The contributor is a female aged 50–59 · the photograph is a close-up of the affected area · the affected area is the arm and head or neck — 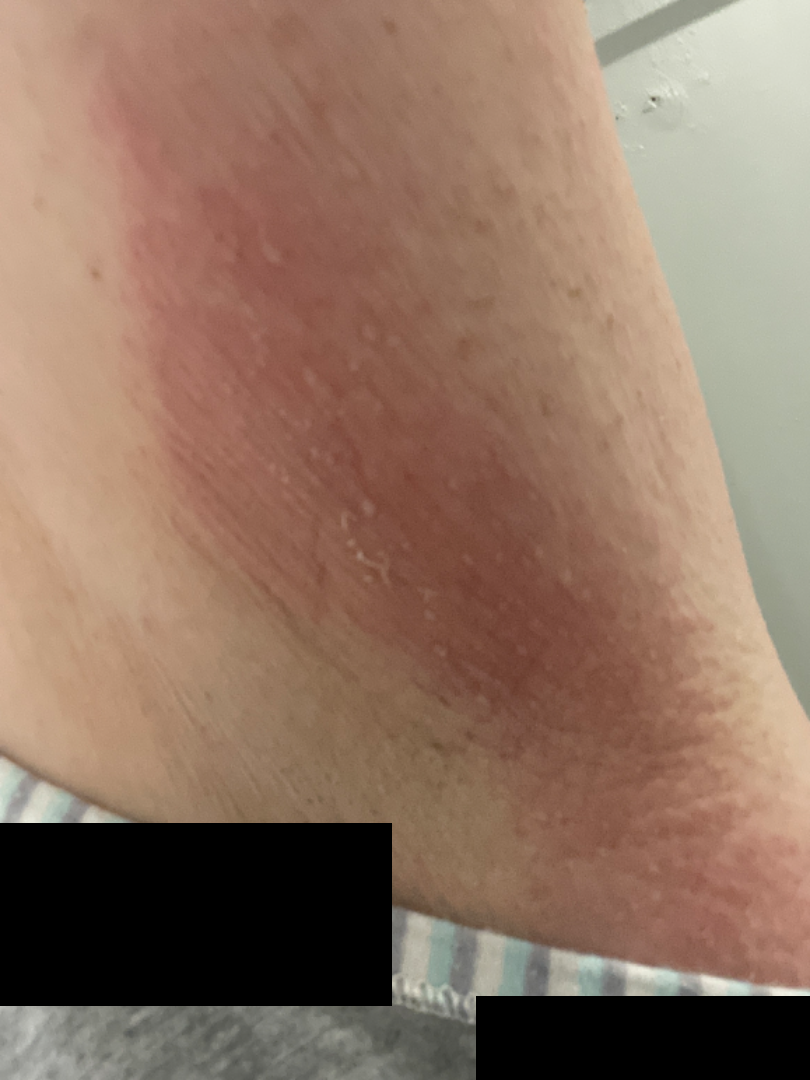Case summary:
- differential diagnosis — Cellulitis (54%); Urticaria (23%); Inflammatory dermatosis (23%)